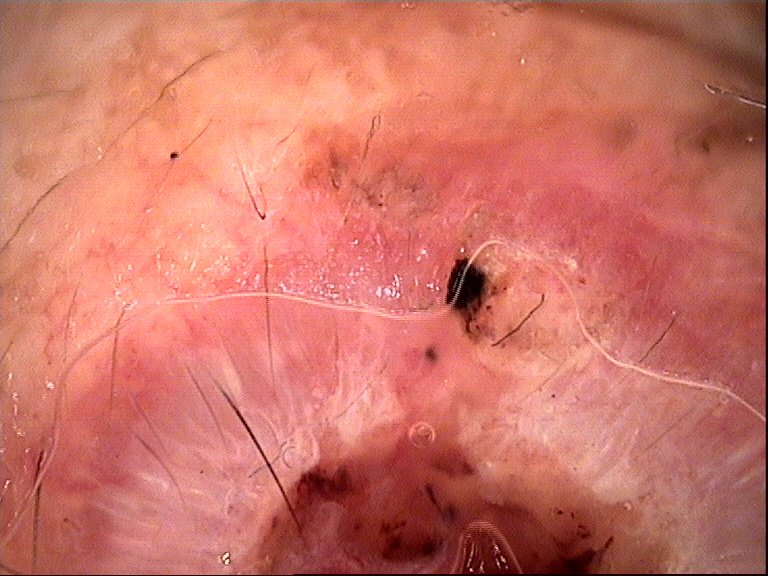Biopsy-confirmed as a basal cell carcinoma.